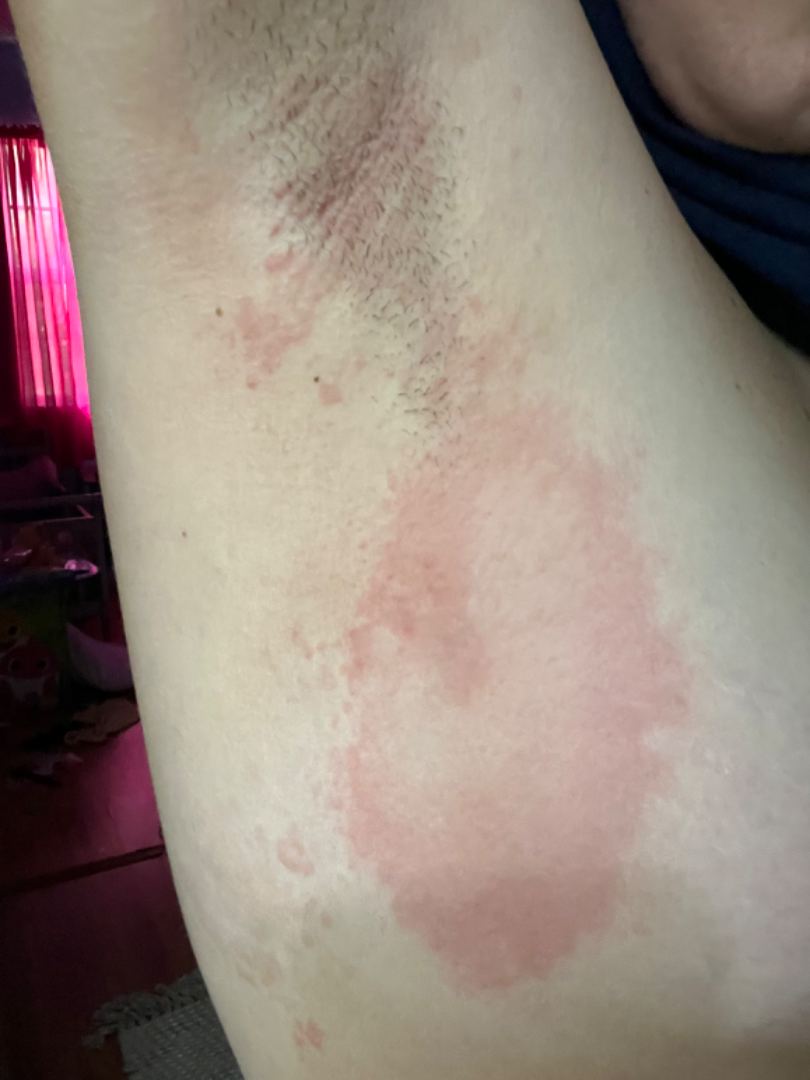Q: Could the case be diagnosed?
A: unable to determine
Q: How was the photo taken?
A: at an angle